The lesion involves the back of the hand, top or side of the foot, front of the torso, head or neck, leg, arm and back of the torso · no associated systemic symptoms reported · the lesion is associated with itching · reported duration is about one day · this is a close-up image · the patient described the issue as a rash: 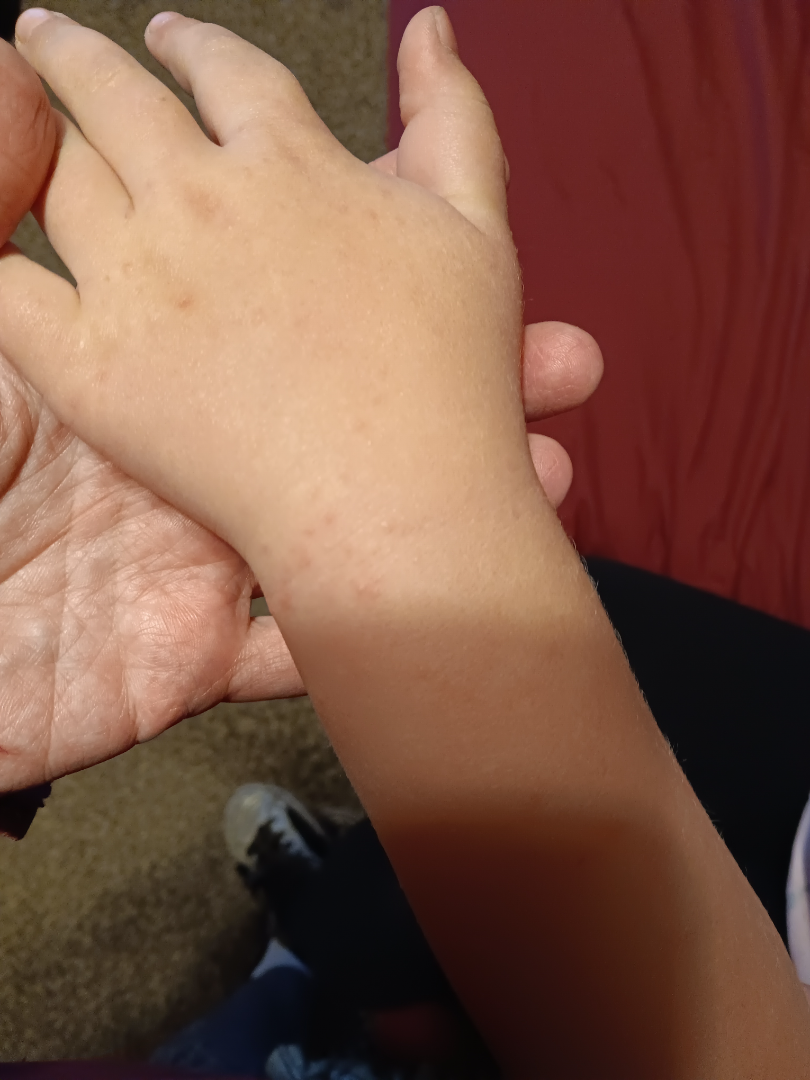Notes:
* assessment: could not be assessed